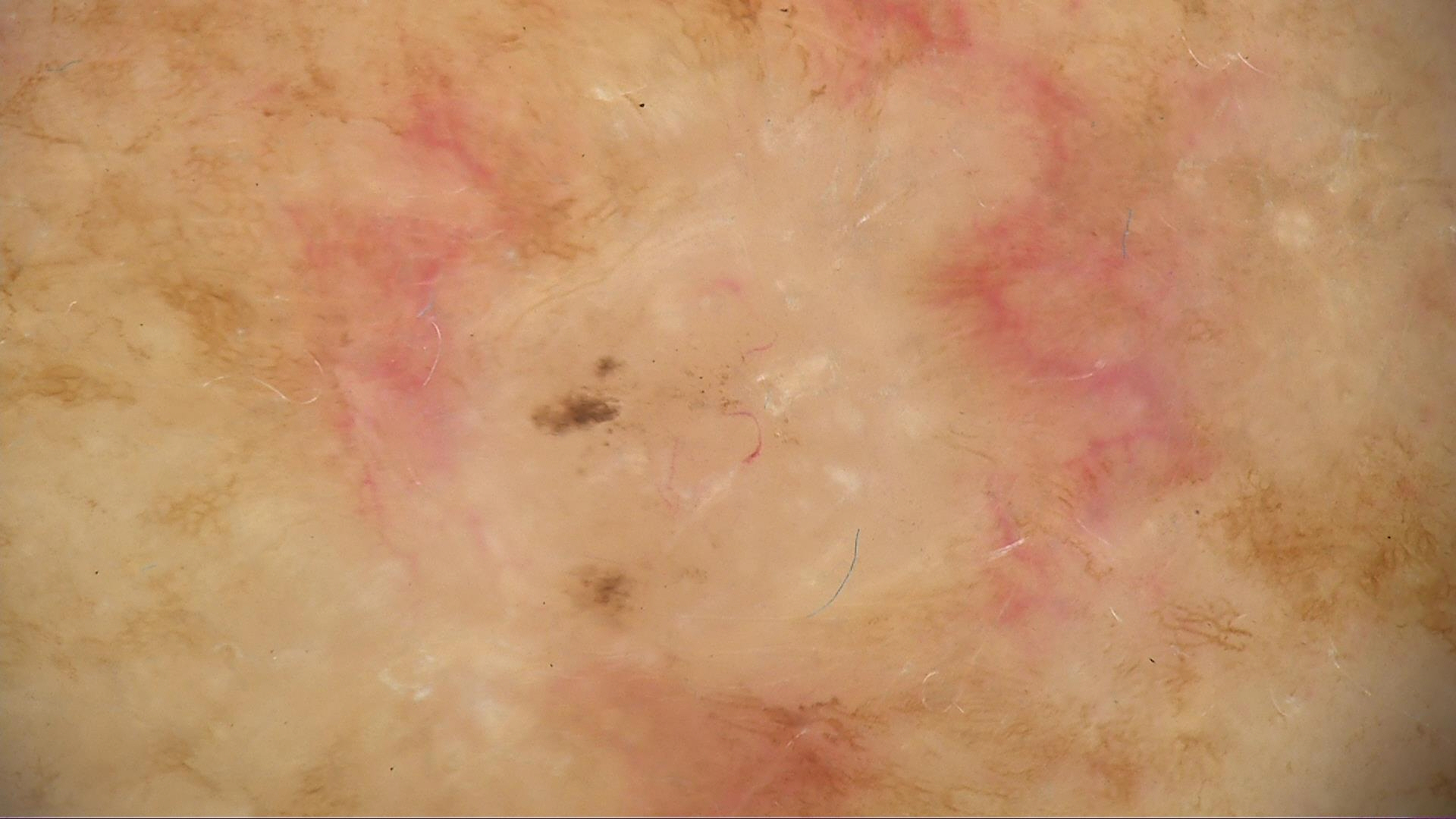diagnostic label = basal cell carcinoma (biopsy-proven).